Texture is reported as flat. The leg is involved. The lesion is associated with bothersome appearance. This image was taken at an angle. No constitutional symptoms were reported. The contributor is 30–39, female:
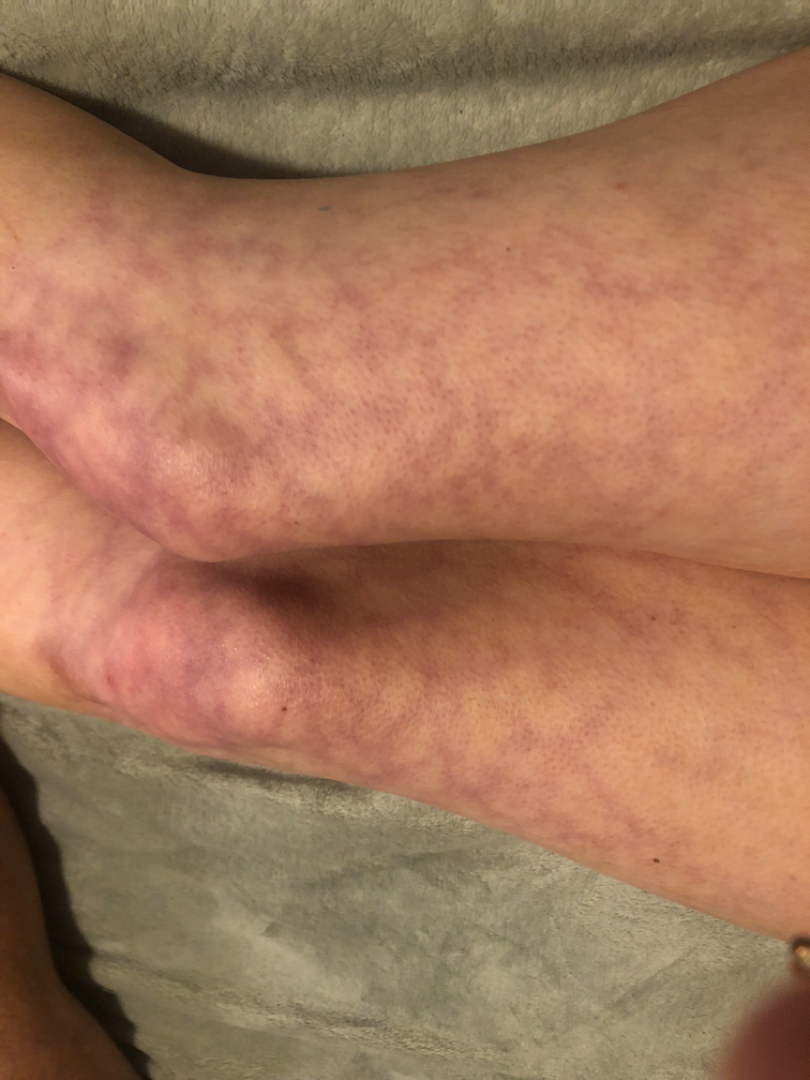On remote review of the image: Livedo reticularis and Erythema ab igne were each considered, in no particular order.